Referred for assessment of suspected melanoma; a moderate number of moles by the patient's own estimate; a female patient age 50; the patient says their skin reddens painfully with sun exposure; a macroscopic clinical photograph of a skin lesion:
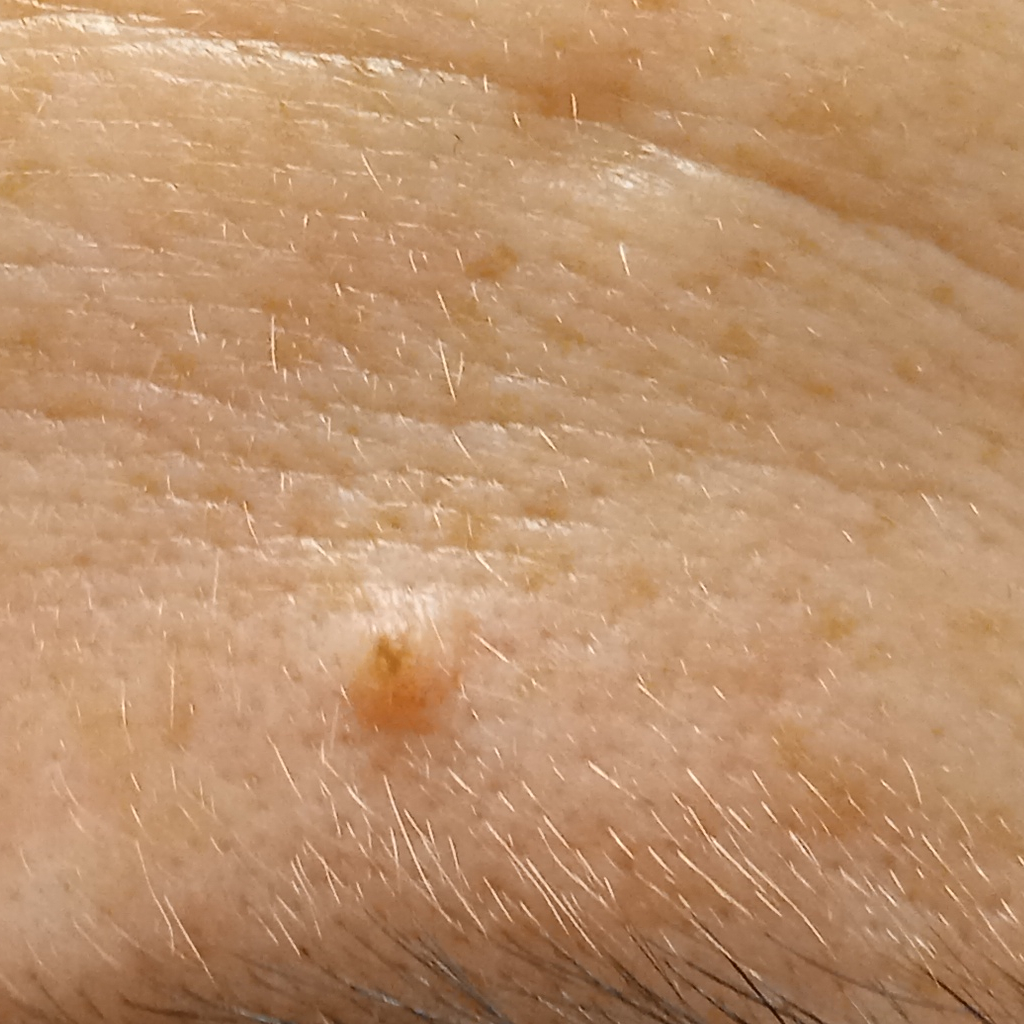The lesion is on the face. The lesion measures approximately 1.8 mm. The lesion was assessed as a melanocytic nevus.